A dermatoscopic image of a skin lesion:
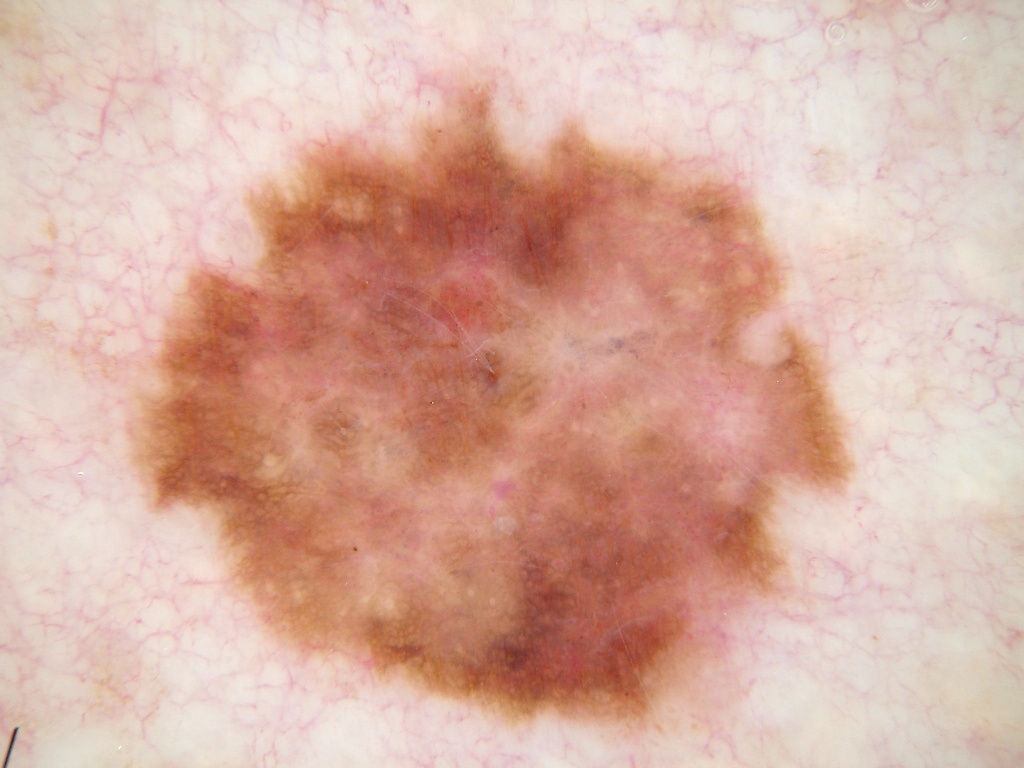Summary: Dermoscopically, the lesion shows no globules or streaks. As (left, top, right, bottom), the lesion occupies the region 124, 80, 851, 738. Impression: The diagnostic assessment was a benign skin lesion.